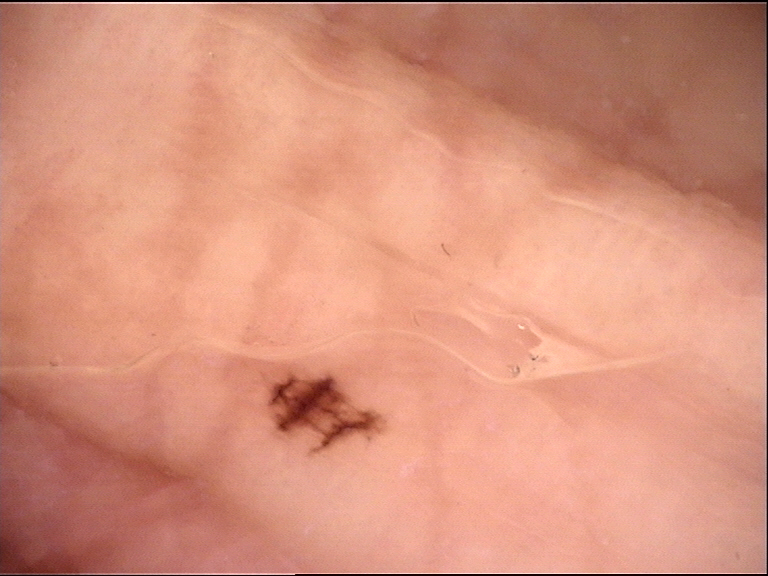Findings: A dermoscopic close-up of a skin lesion. Conclusion: Consistent with a banal lesion — an acral junctional nevus.